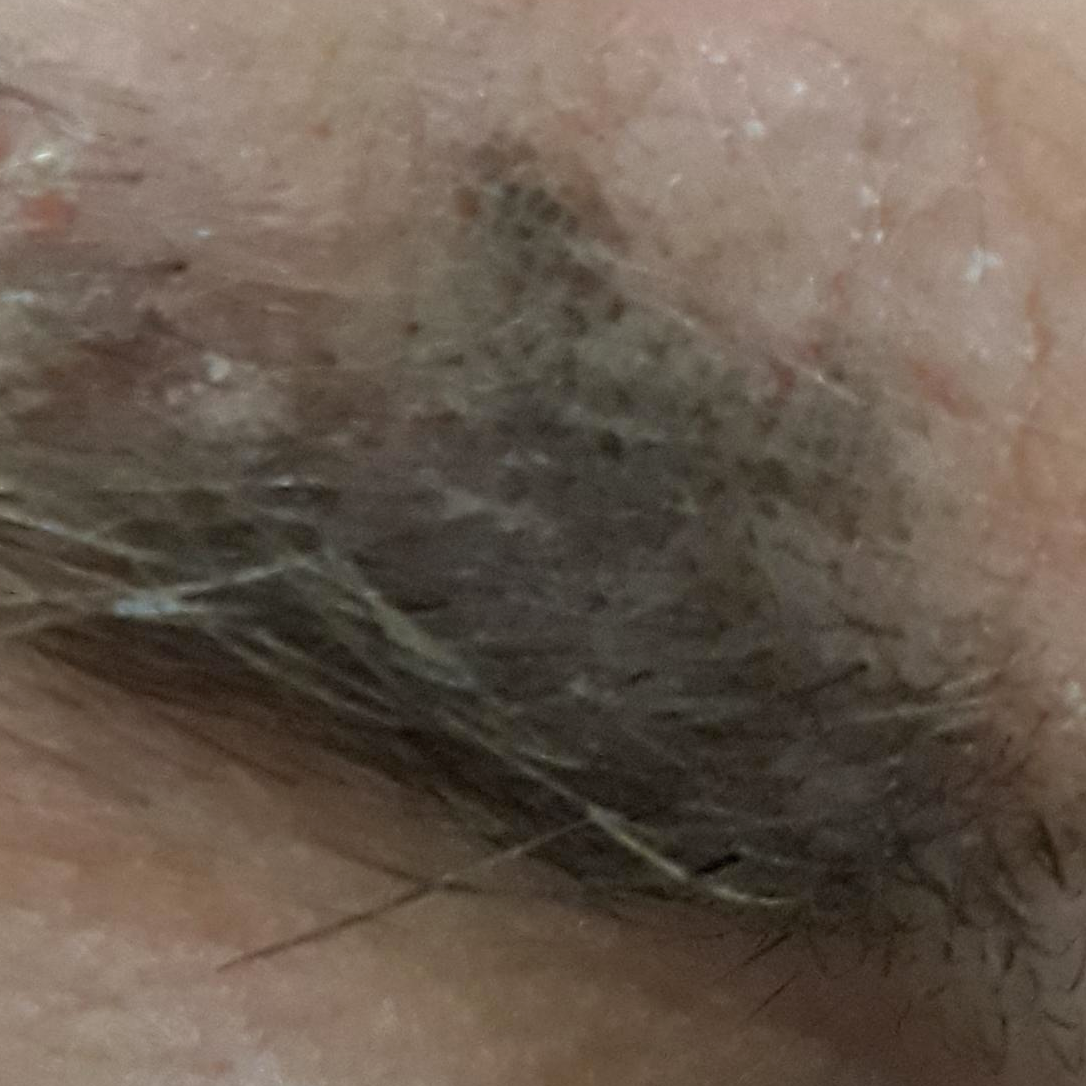{
  "symptoms": {
    "present": [
      "growth",
      "elevation"
    ]
  },
  "diagnosis": {
    "name": "seborrheic keratosis",
    "code": "SEK",
    "malignancy": "benign",
    "confirmation": "clinical consensus"
  }
}